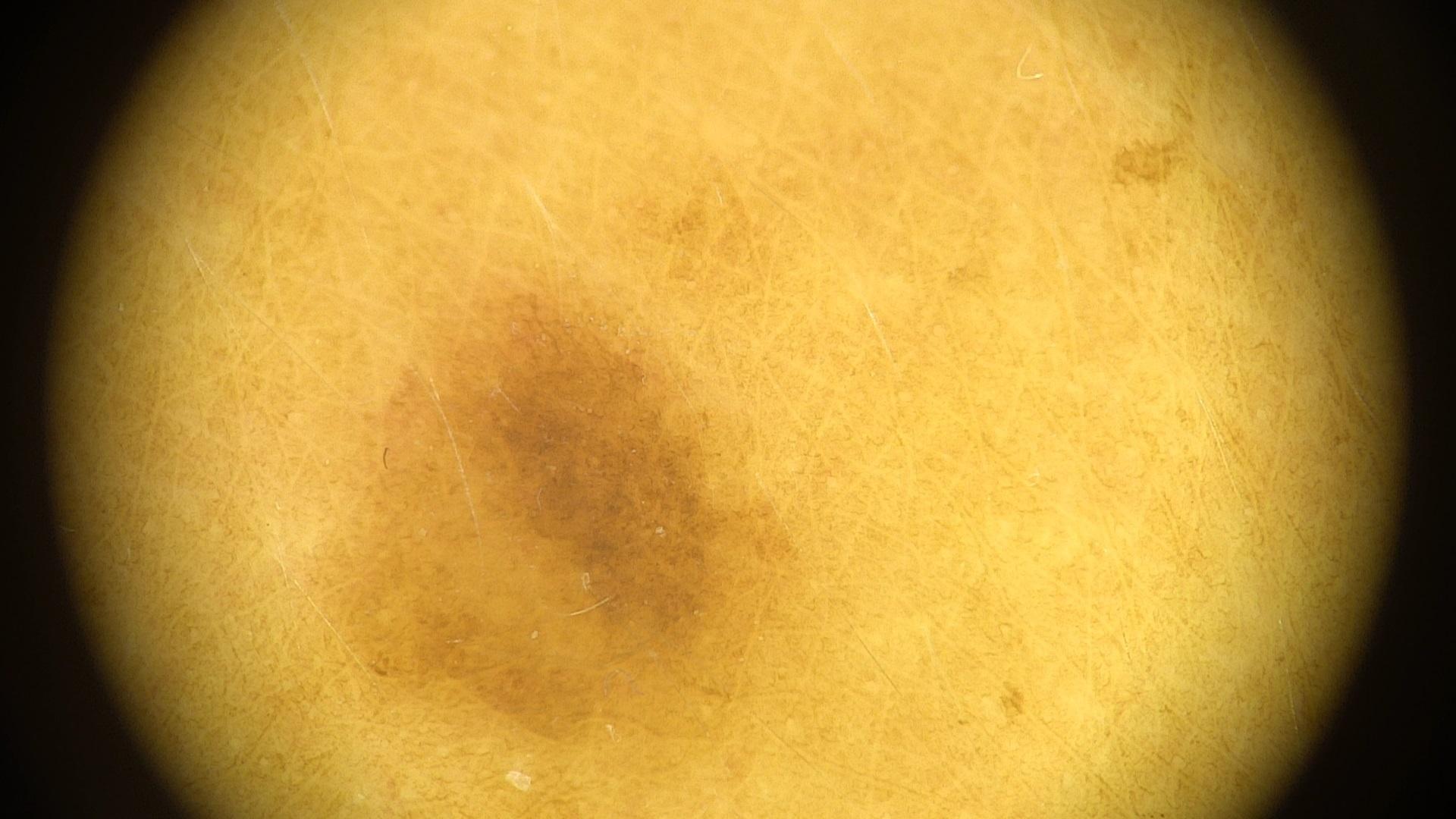subject — female, aged 33 to 37; modality — contact-polarized dermoscopy; skin type — II; body site — the trunk; impression — Nevus.